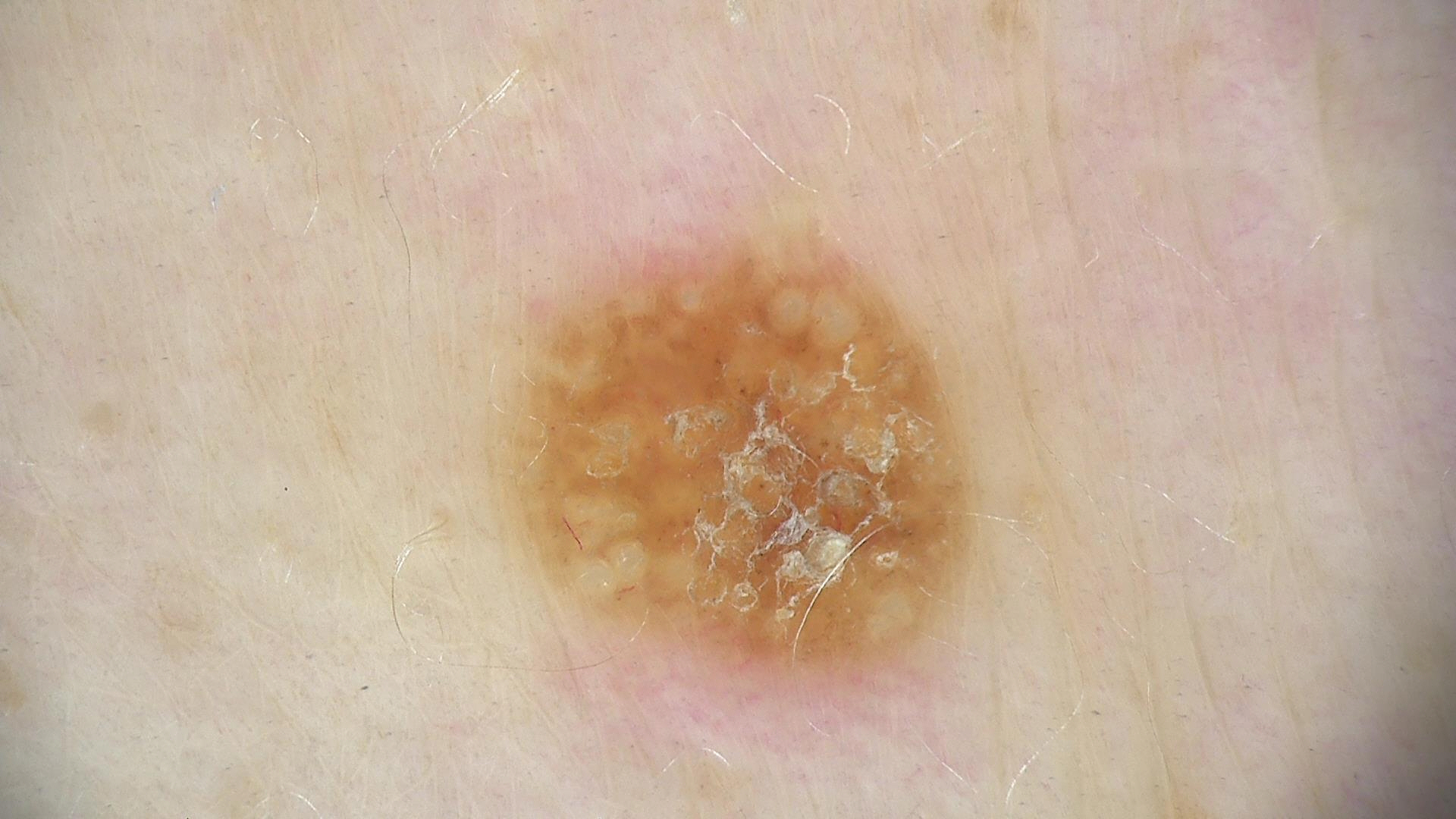Conclusion:
Classified as a seborrheic keratosis.